The photograph was taken at an angle. Located on the sole of the foot.
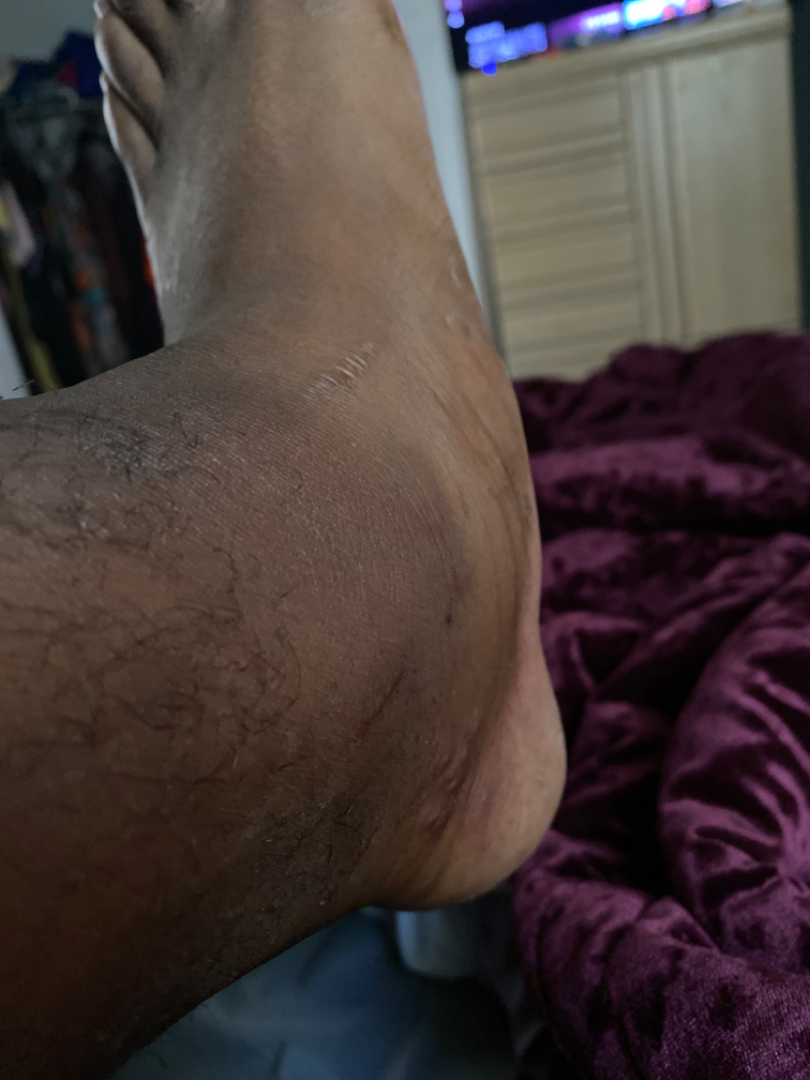assessment: not assessable; history: less than one week; patient describes the issue as: a rash.